A dermoscopic close-up of a skin lesion · a female subject, aged approximately 25: 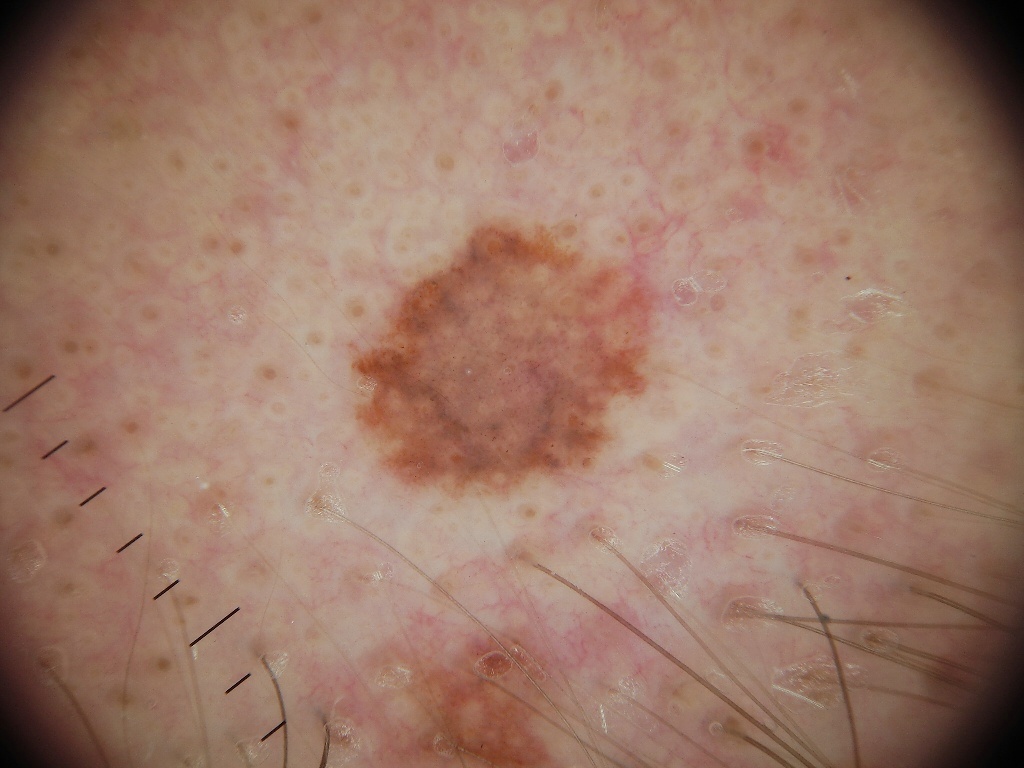The lesion is small relative to the field of view. The lesion spans bbox(350, 220, 654, 494). Dermoscopic review identifies milia-like cysts; no pigment network, negative network, globules, or streaks. Clinically diagnosed as a melanocytic nevus.